This is a close-up image · female patient, age 18–29 · the lesion involves the back of the torso and front of the torso:
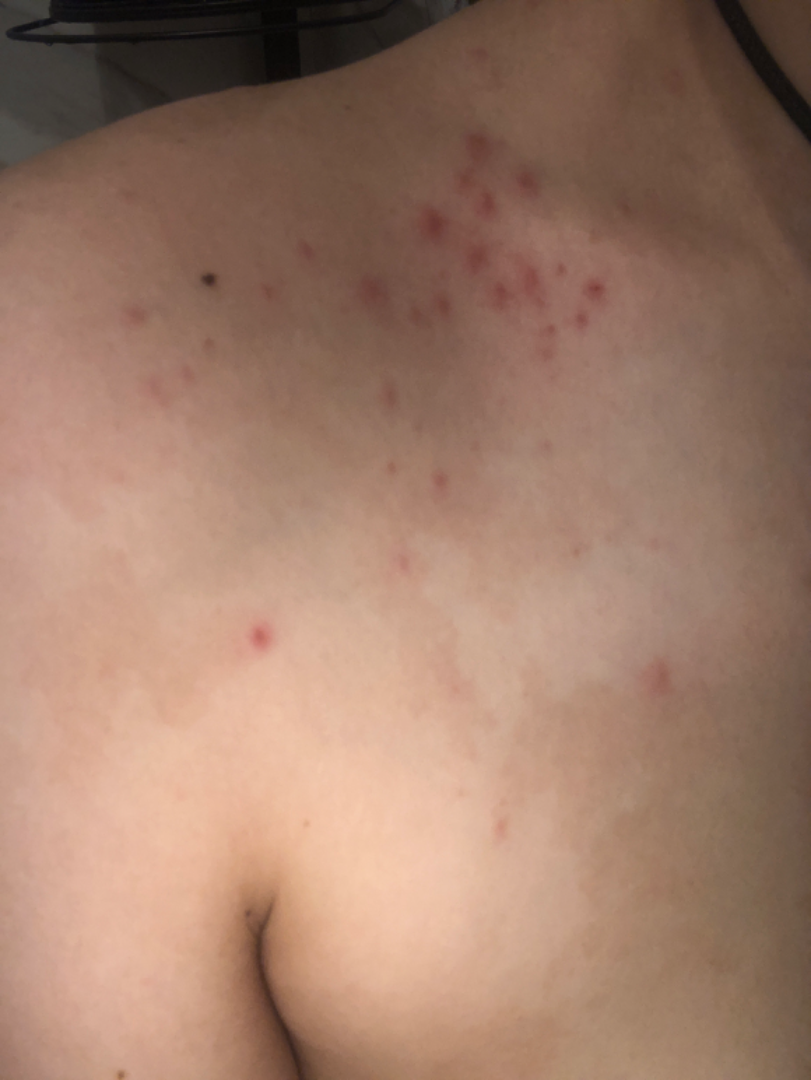<dermatology_case>
  <assessment>indeterminate from the photograph</assessment>
  <duration>about one day</duration>
  <texture>raised or bumpy</texture>
  <skin_tone>
    <fitzpatrick>II</fitzpatrick>
  </skin_tone>
  <systemic_symptoms>none reported</systemic_symptoms>
</dermatology_case>